A dermoscopic close-up of a skin lesion:
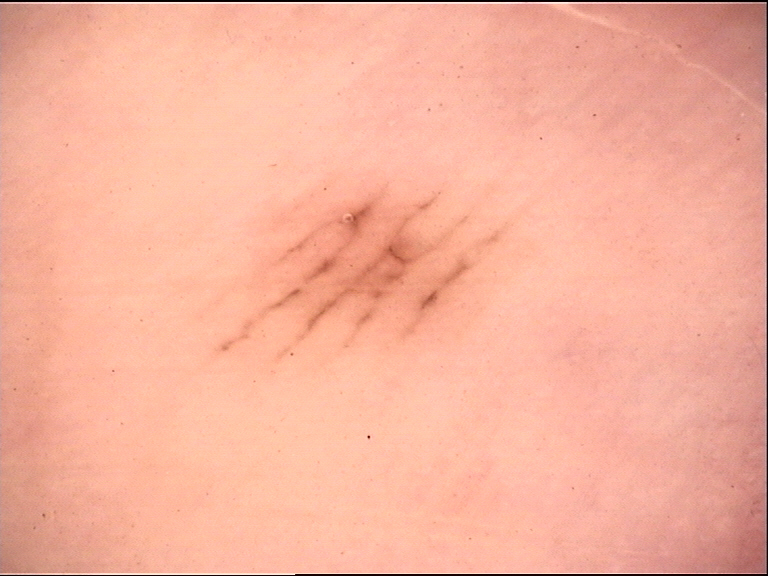subtype: banal, diagnosis: acral junctional nevus (expert consensus).